The photo was captured at an angle — 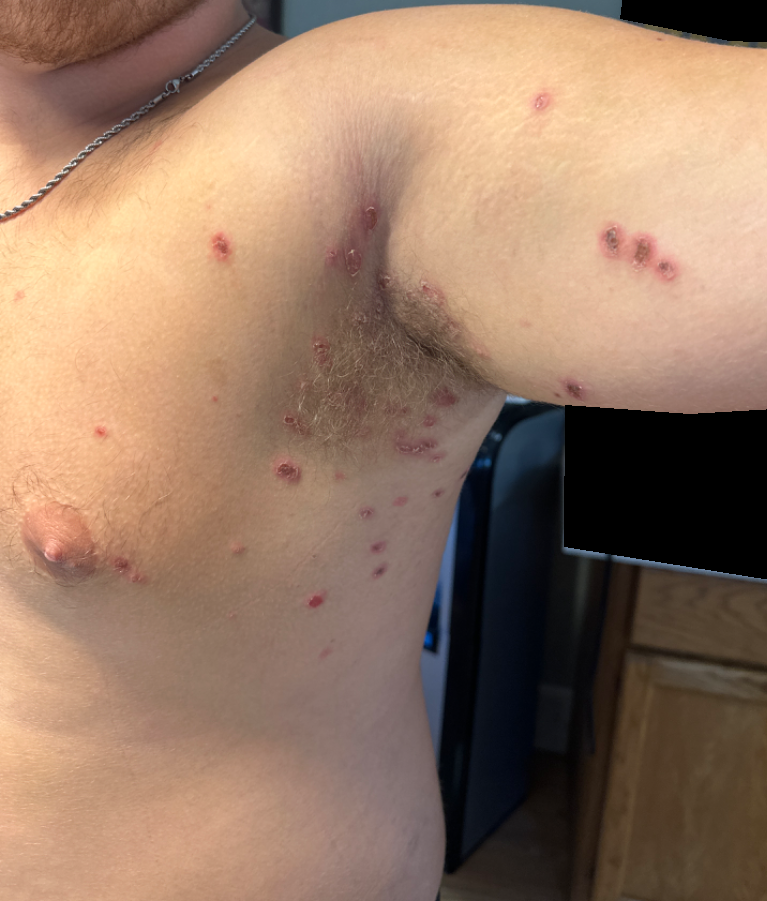Case summary:
• dermatologist impression: in keeping with Impetigo